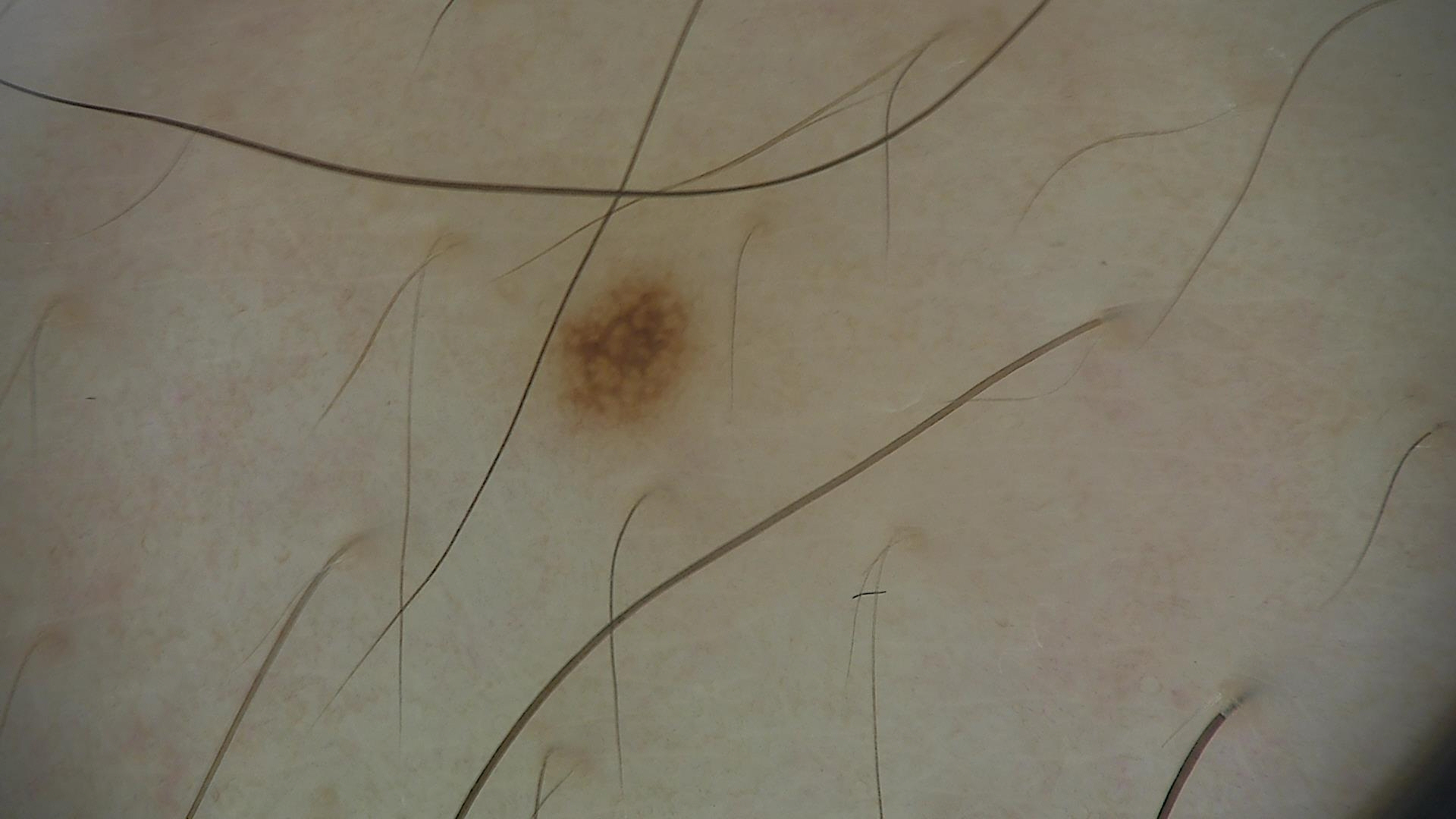Q: What kind of image is this?
A: dermatoscopy
Q: What is this lesion?
A: dysplastic junctional nevus (expert consensus)